This is a close-up image — 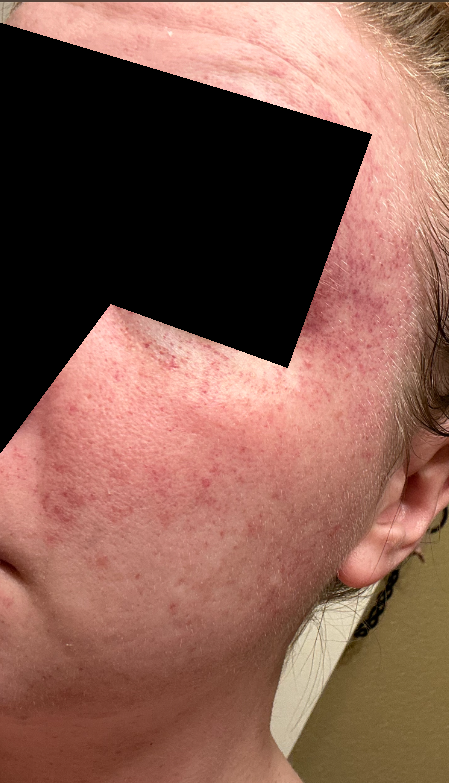The reviewing dermatologist's impression was: the favored diagnosis is Rosacea; possibly Acne; also on the differential is Cutaneous lupus.